Fitzpatrick phototype III; lay graders estimated 2 on the MST. The photo was captured at a distance.
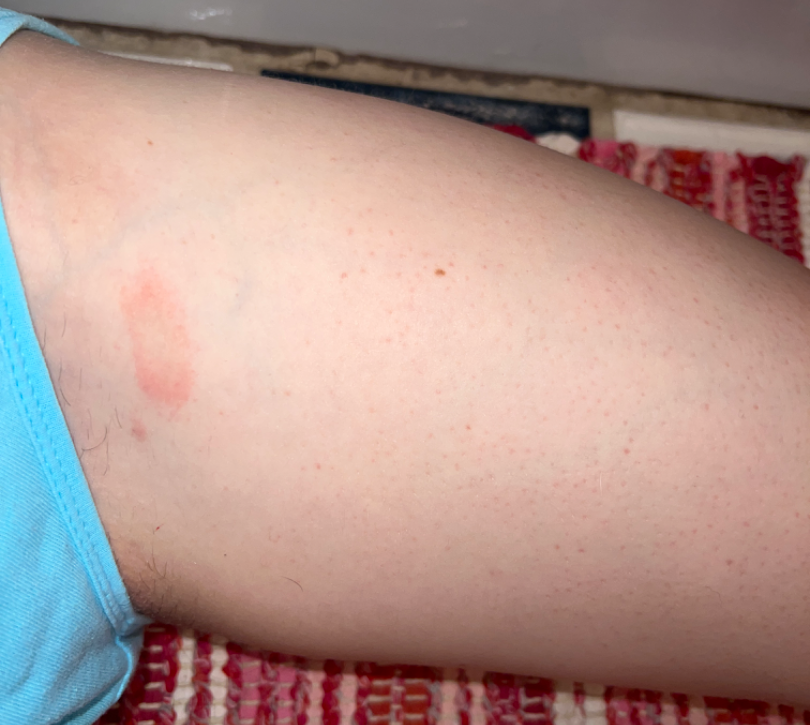Impression: The case was difficult to assess from the available photograph.